A close-up photograph. Located on the leg. The contributor is 18–29, male: 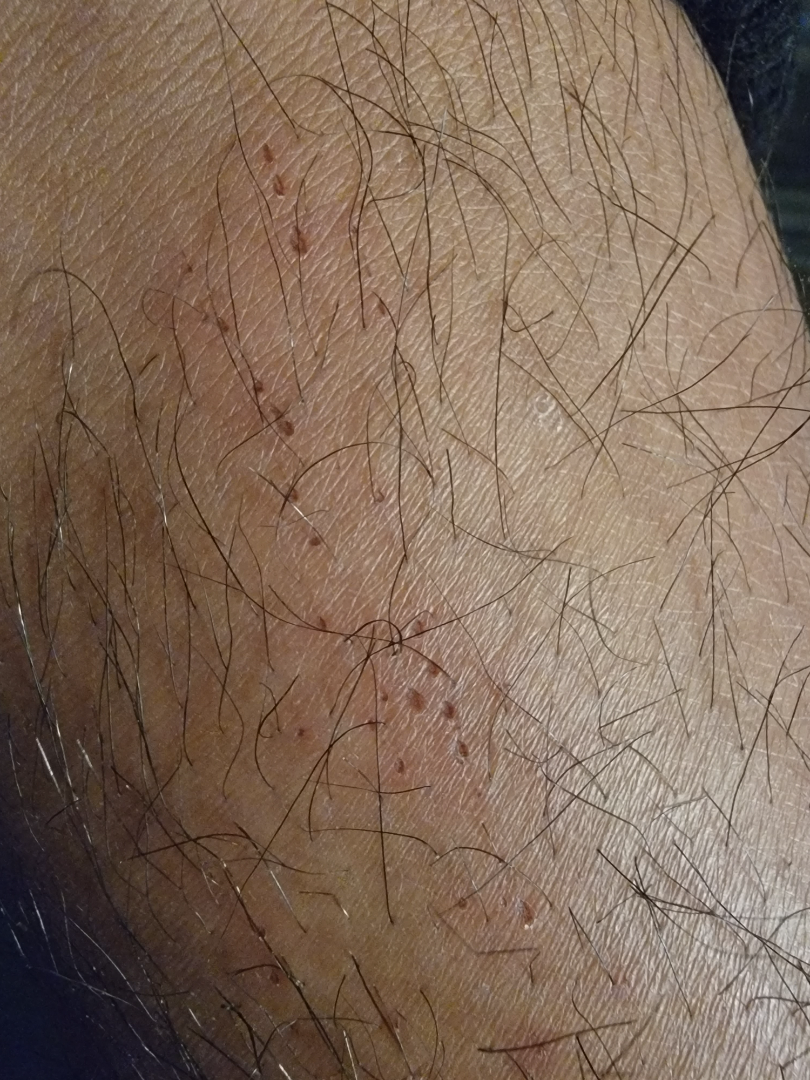{
  "assessment": "unable to determine",
  "duration": "less than one week",
  "texture": "rough or flaky",
  "patient_category": "a rash",
  "skin_tone": {
    "fitzpatrick": "V"
  },
  "symptoms": [
    "burning",
    "bothersome appearance"
  ]
}